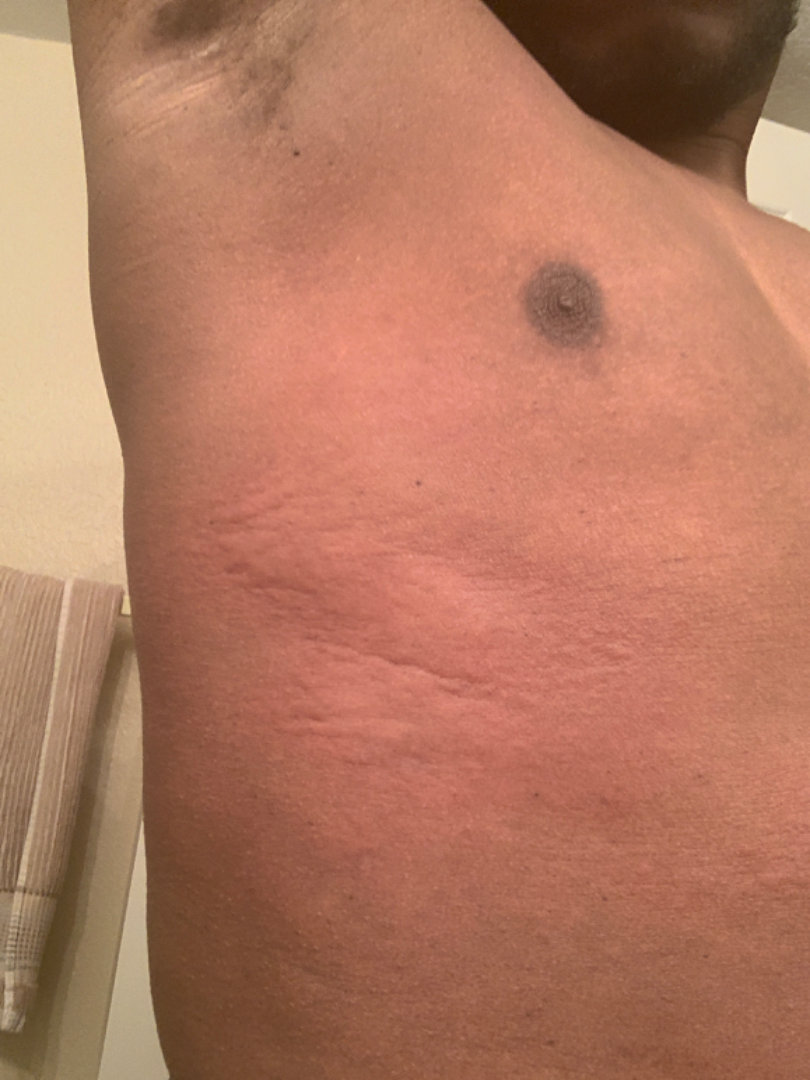Case summary:
- framing: close-up
- subject: male, age 30–39
- location: front of the torso and leg
- differential: Urticaria (0.86); Allergic Contact Dermatitis (0.14)